The patient reports a family history of skin cancer, a personal history of skin cancer, a personal history of cancer, no immunosuppression, and no prior organ transplant; the patient says their skin tans without first burning; a dermoscopy image of a skin lesion; a female patient 58 years of age; the patient describes having a moderate number of moles; imaged for a research study, with no referral diagnosis recorded — 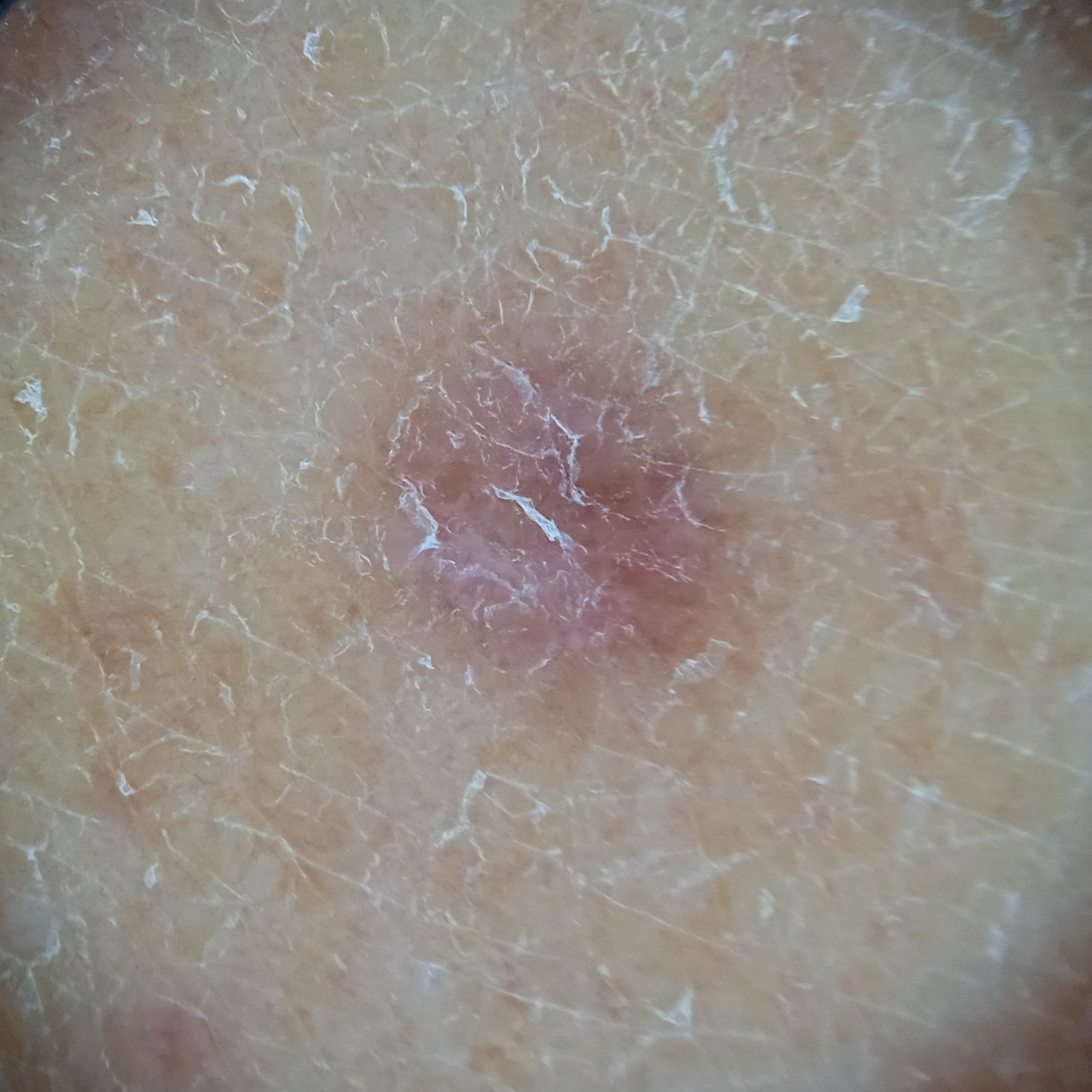The lesion involves a leg.
The lesion measures approximately 5.2 mm.
Reviewed by four dermatologists, the consensus diagnosis was a dermatofibroma; the reviewers were moderately confident; an alternative consideration was a histiocytoma and a melanocytic nevus.